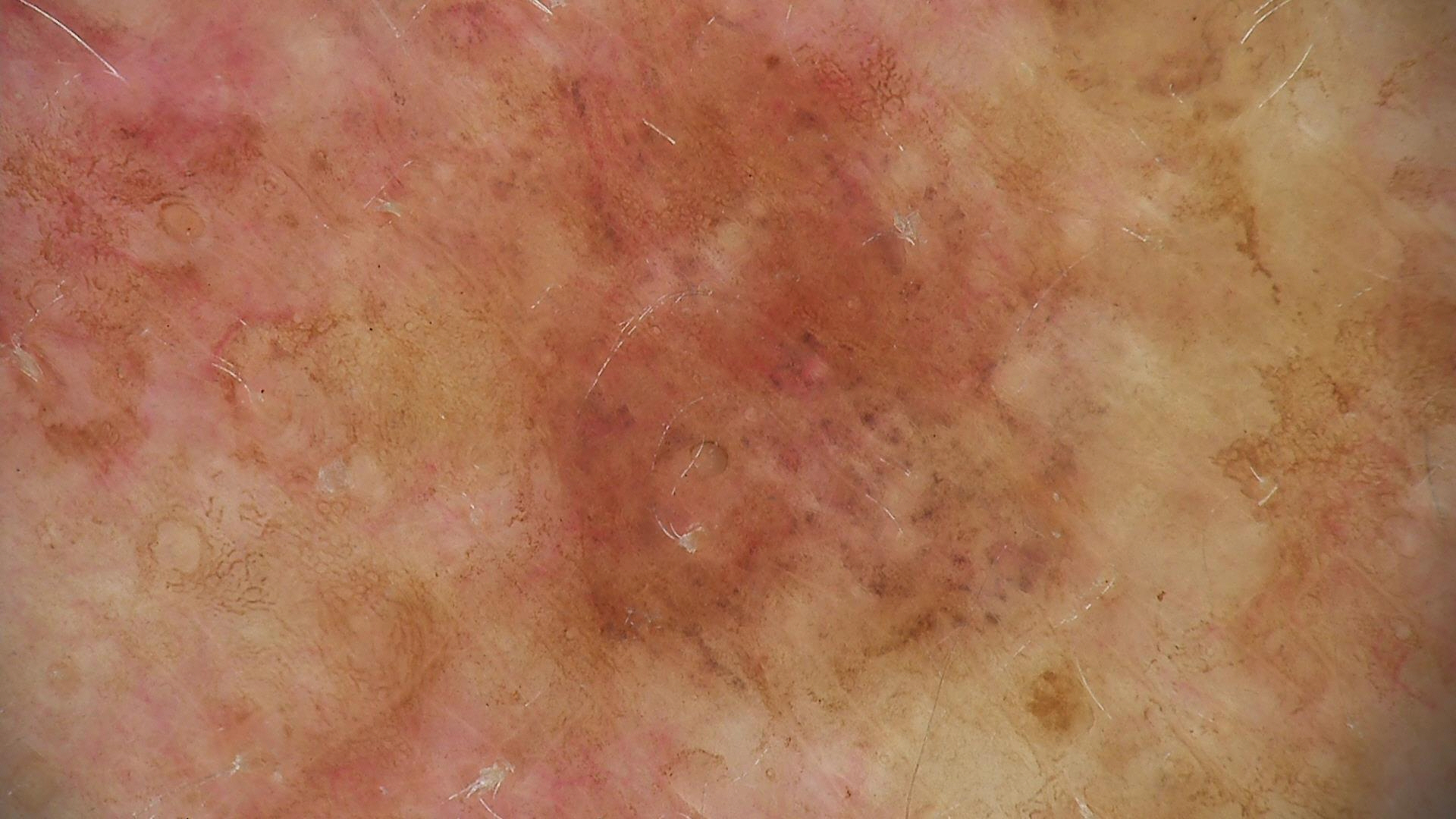The diagnosis was a keratinocytic lesion — a lichenoid keratosis.